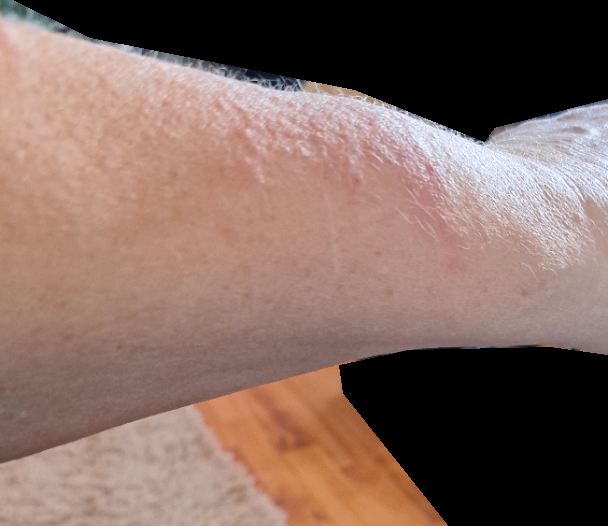The arm is involved. Female contributor, age 60–69. Symptoms reported: itching. This image was taken at a distance. Present for one to four weeks. Texture is reported as raised or bumpy. Allergic Contact Dermatitis (possible); Irritant Contact Dermatitis (possible).